Dermoscopy of a skin lesion: 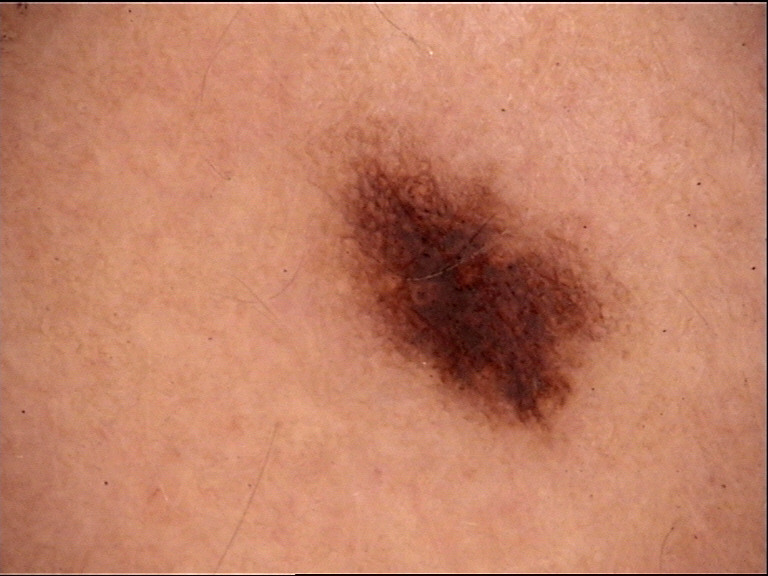category = banal | diagnosis = junctional nevus (expert consensus).